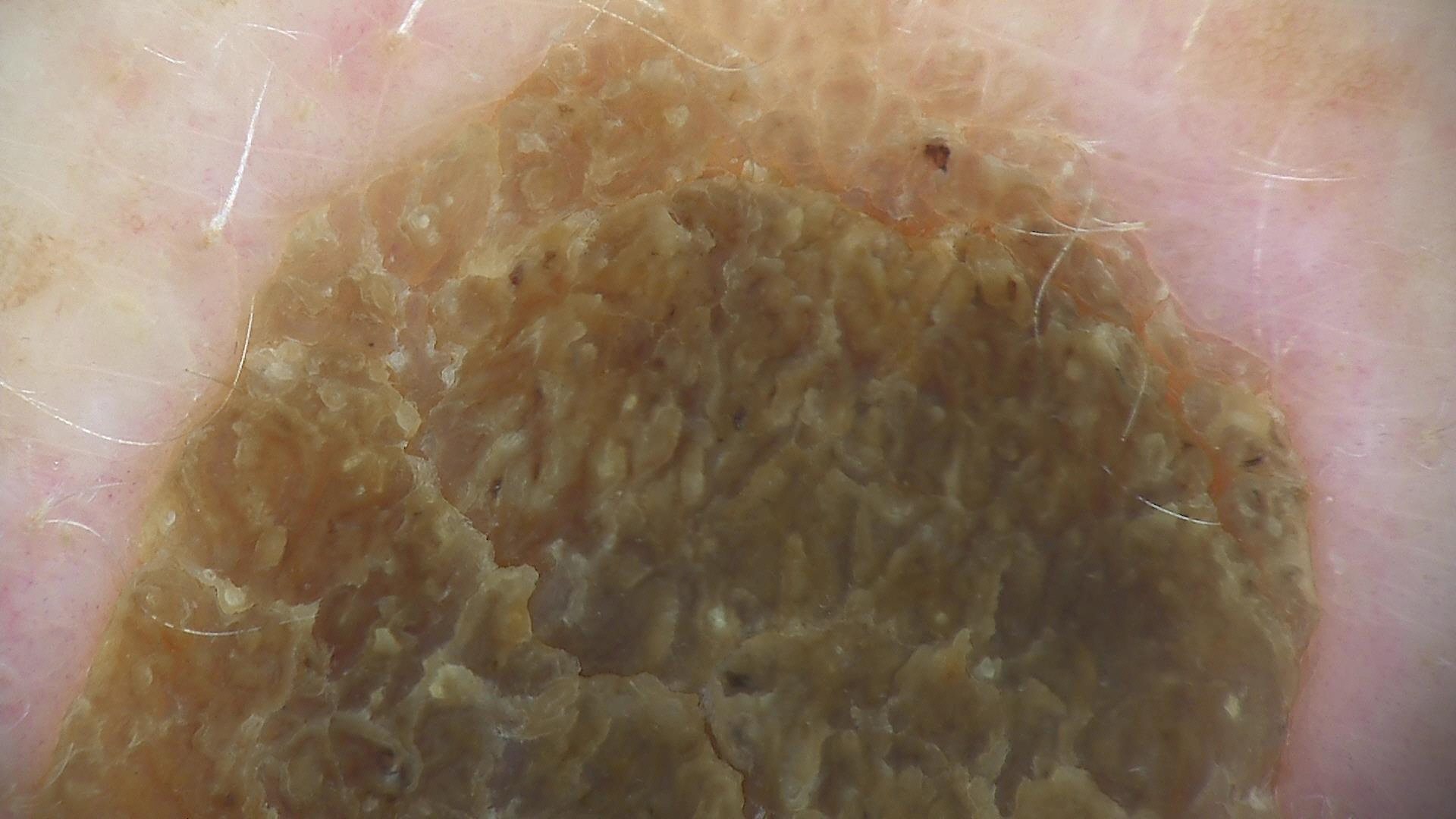Impression:
Classified as a seborrheic keratosis.